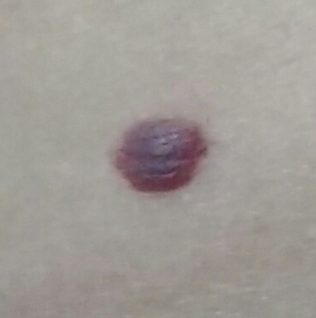Summary:
A patient 59 years of age.
Conclusion:
The diagnostic impression was a nevus.